The photo was captured at an angle.
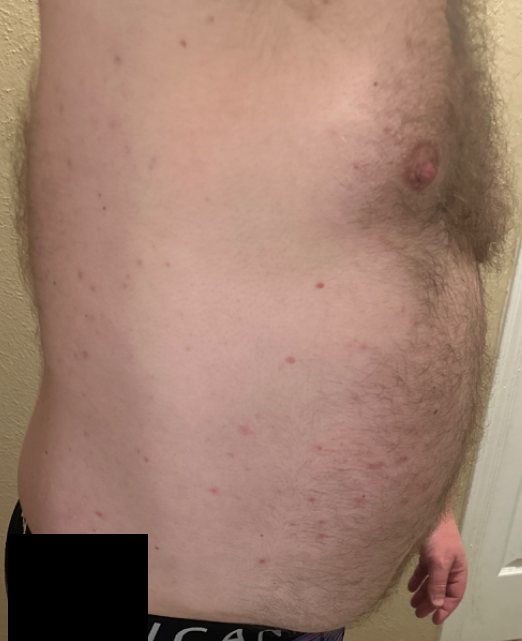The case was indeterminate on photographic review.